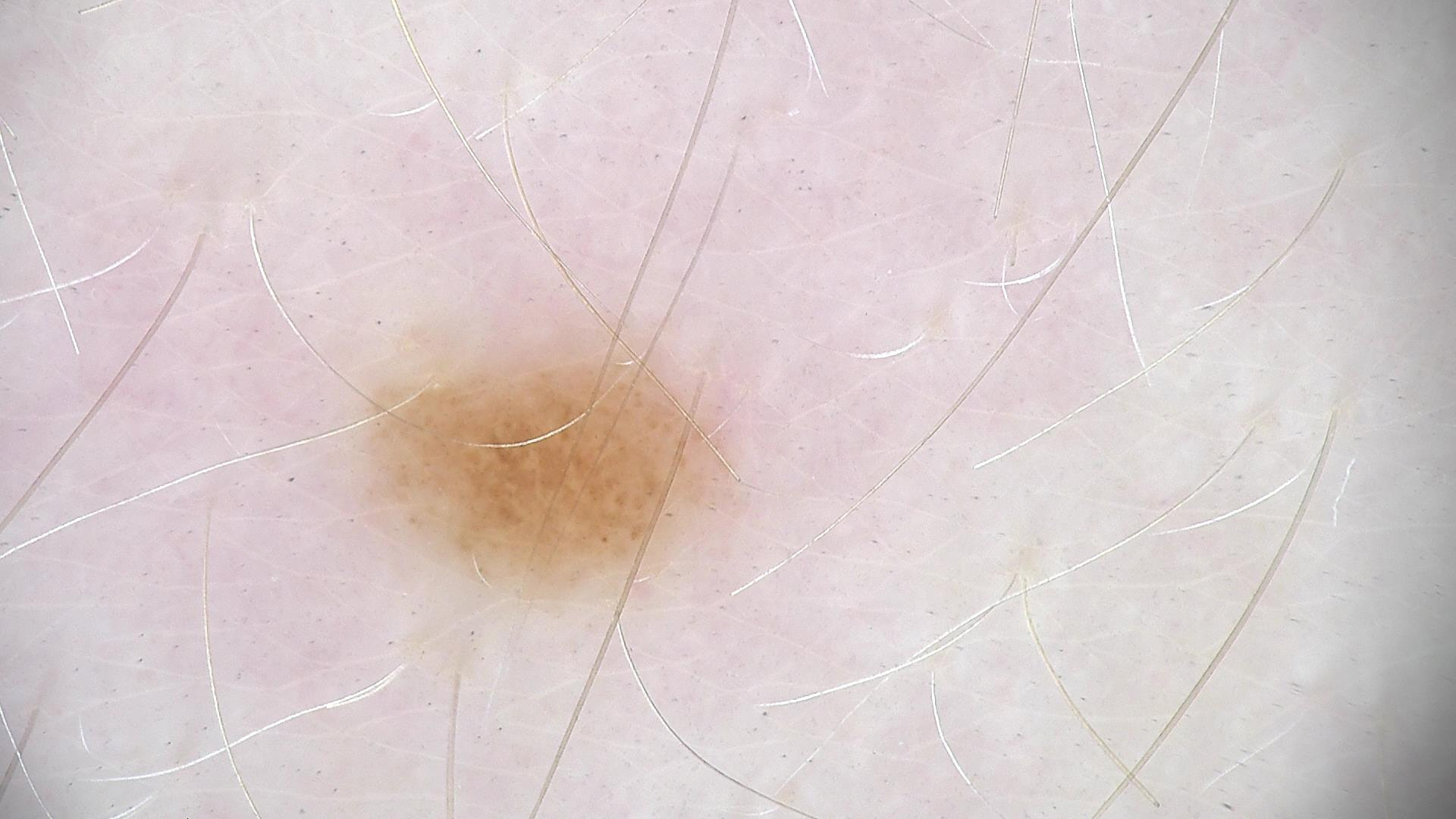assessment = dysplastic junctional nevus (expert consensus).